The photo was captured at a distance, the leg is involved:
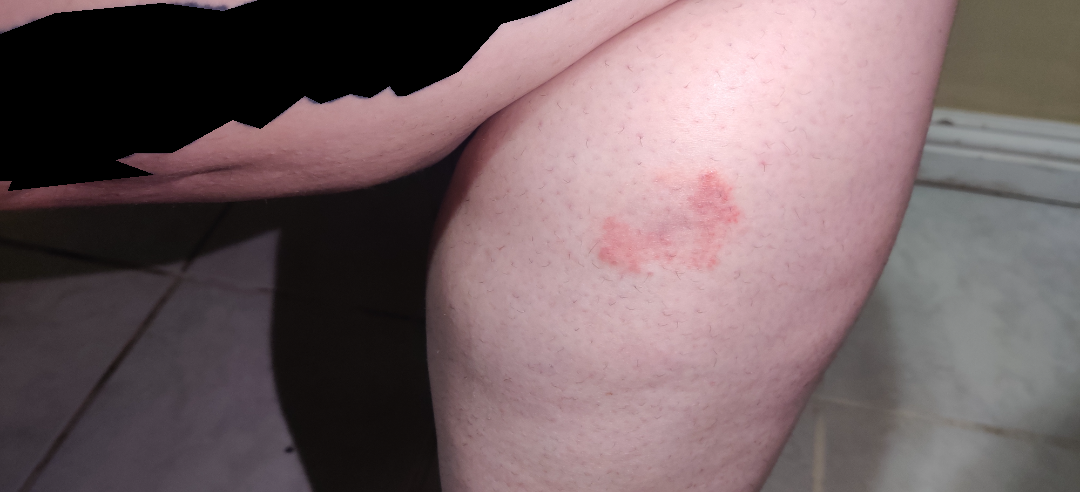The image was not sufficient for the reviewer to characterize the skin condition. No constitutional symptoms were reported. Symptoms reported: enlargement, bothersome appearance and itching.